The affected area is the back of the torso, back of the hand, front of the torso and arm; the photo was captured at a distance: 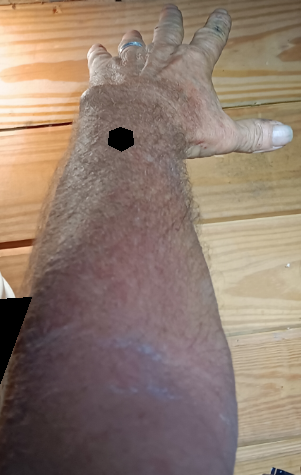The dermatologist could not determine a likely condition from the photograph alone.
The lesion is associated with darkening, itching and bothersome appearance.
No constitutional symptoms were reported.
The condition has been present for less than one week.
The lesion is described as rough or flaky and raised or bumpy.